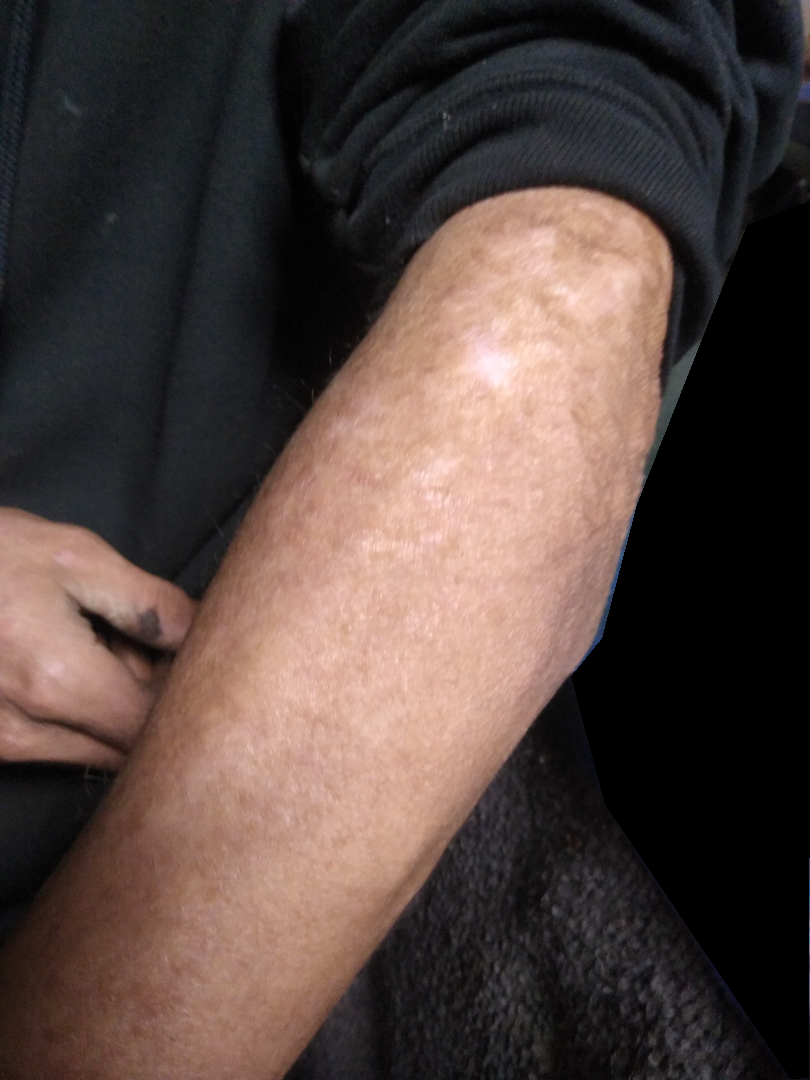Human graders estimated Monk skin tone scale 3 or 4. The photo was captured at an angle.